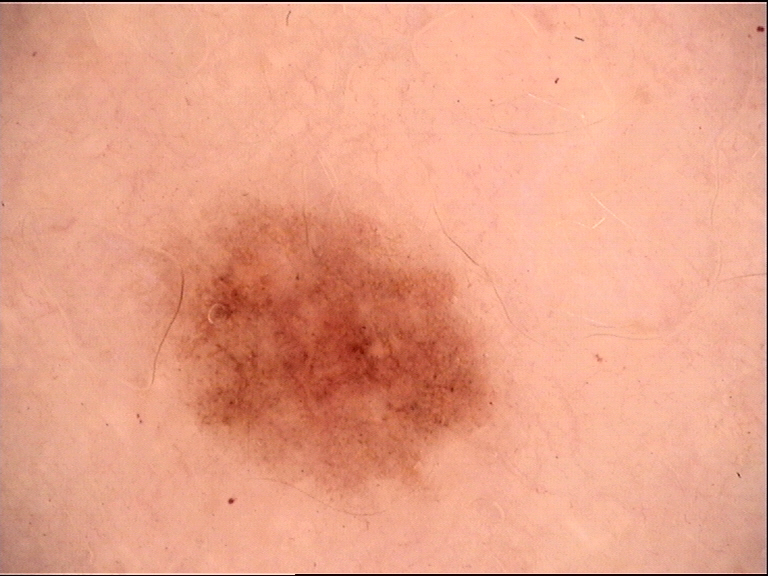assessment: dysplastic junctional nevus (expert consensus)